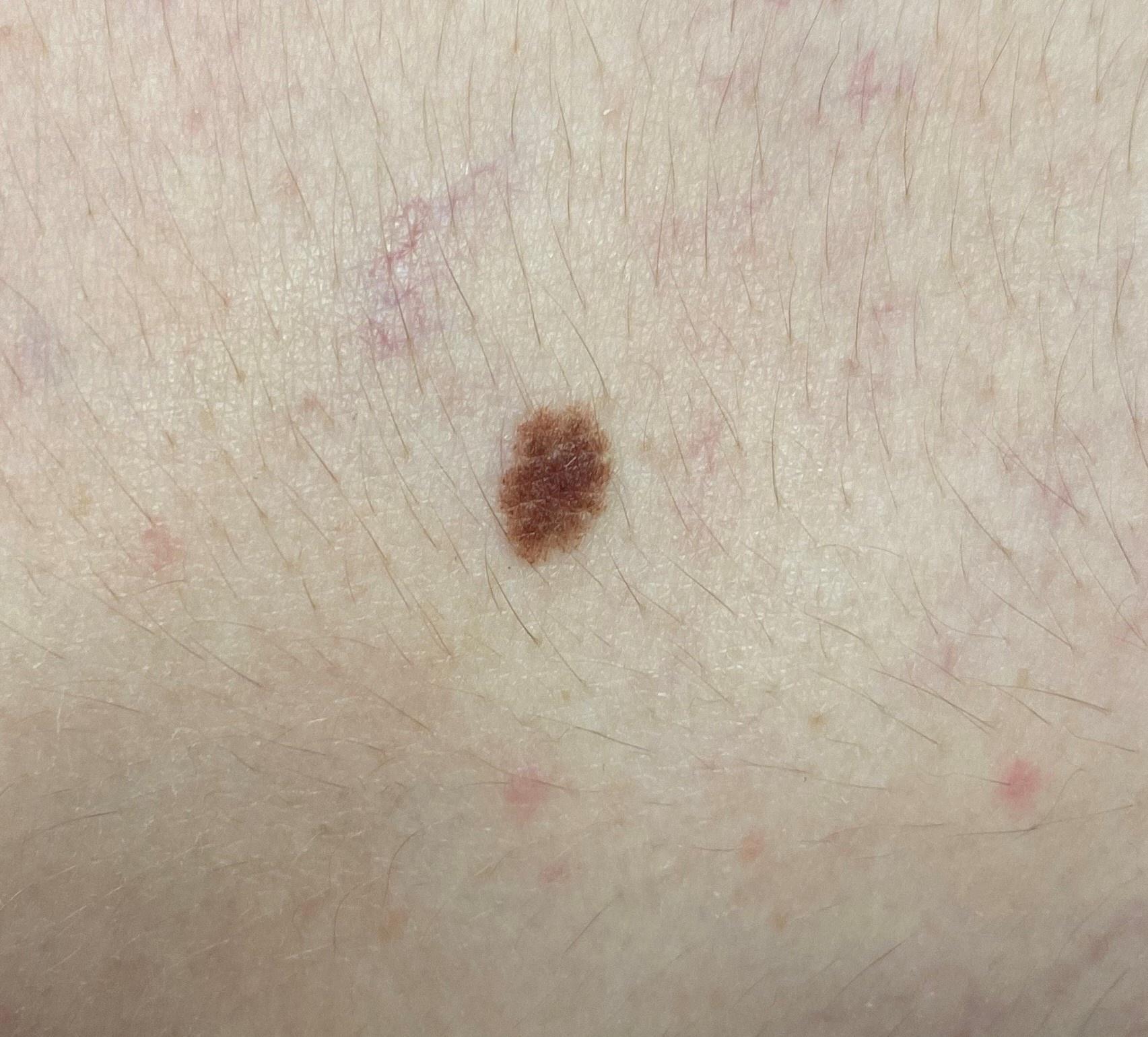Clinical context: A clinical photograph of a skin lesion. Pathology: On biopsy, the diagnosis was a nevus.